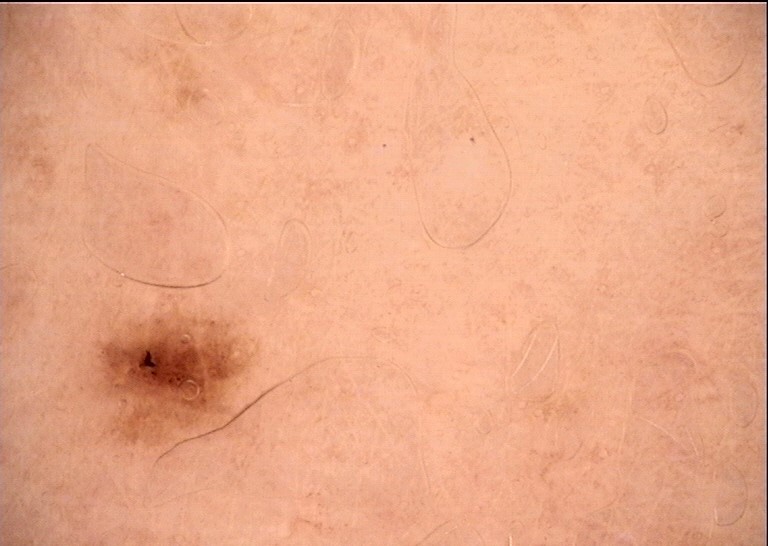Summary:
Dermoscopy of a skin lesion.
Conclusion:
The diagnosis was a banal lesion — a junctional nevus.